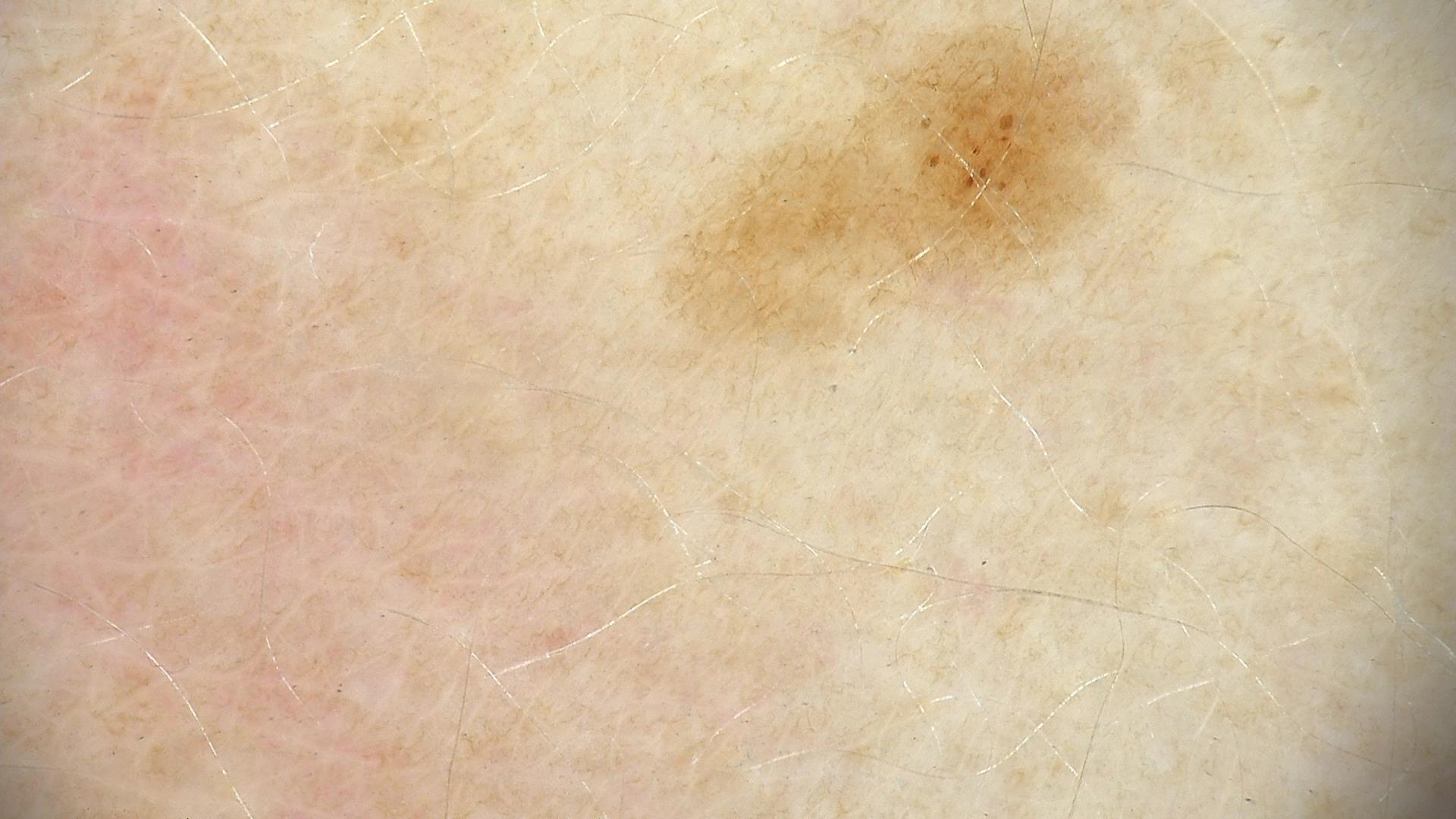Conclusion: Consistent with a dysplastic junctional nevus.